A dermoscopic photograph of a skin lesion.
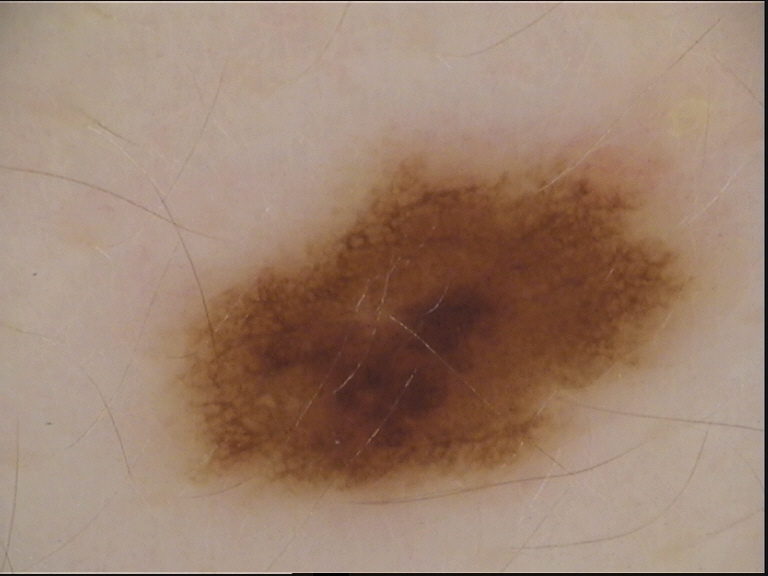Consistent with a dysplastic junctional nevus.